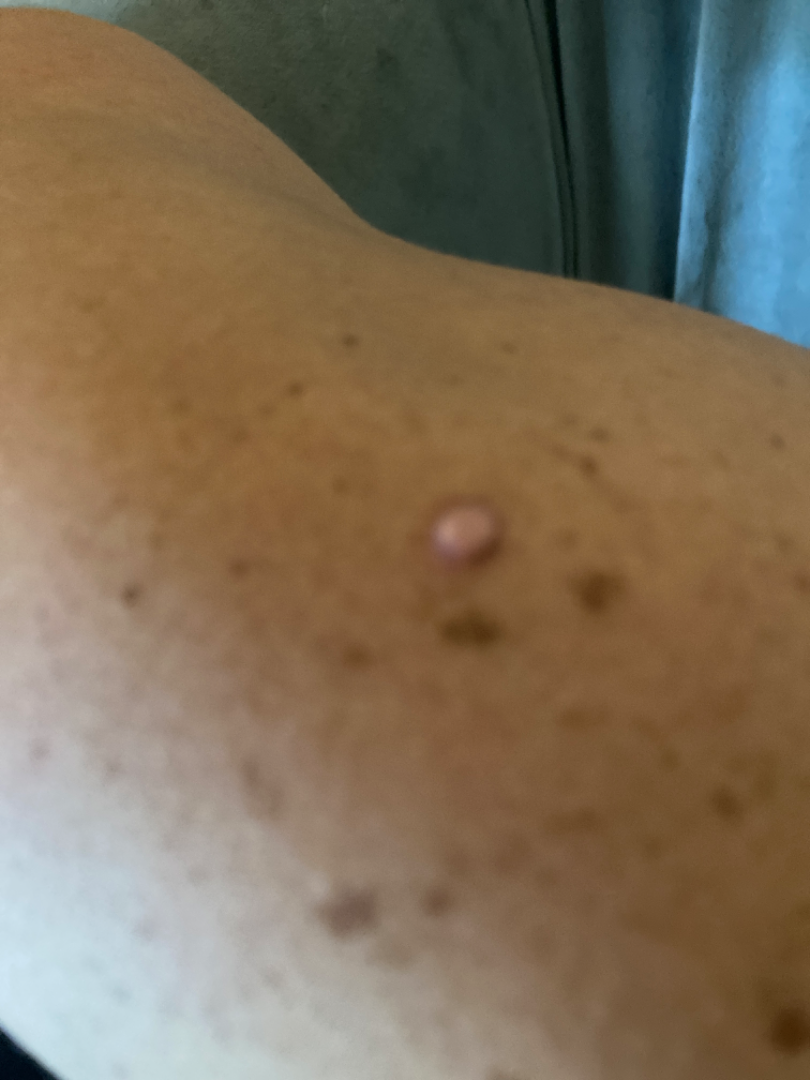<dermatology_case>
  <assessment>unable to determine</assessment>
</dermatology_case>